A male subject roughly 55 years of age; a dermatoscopic image of a skin lesion.
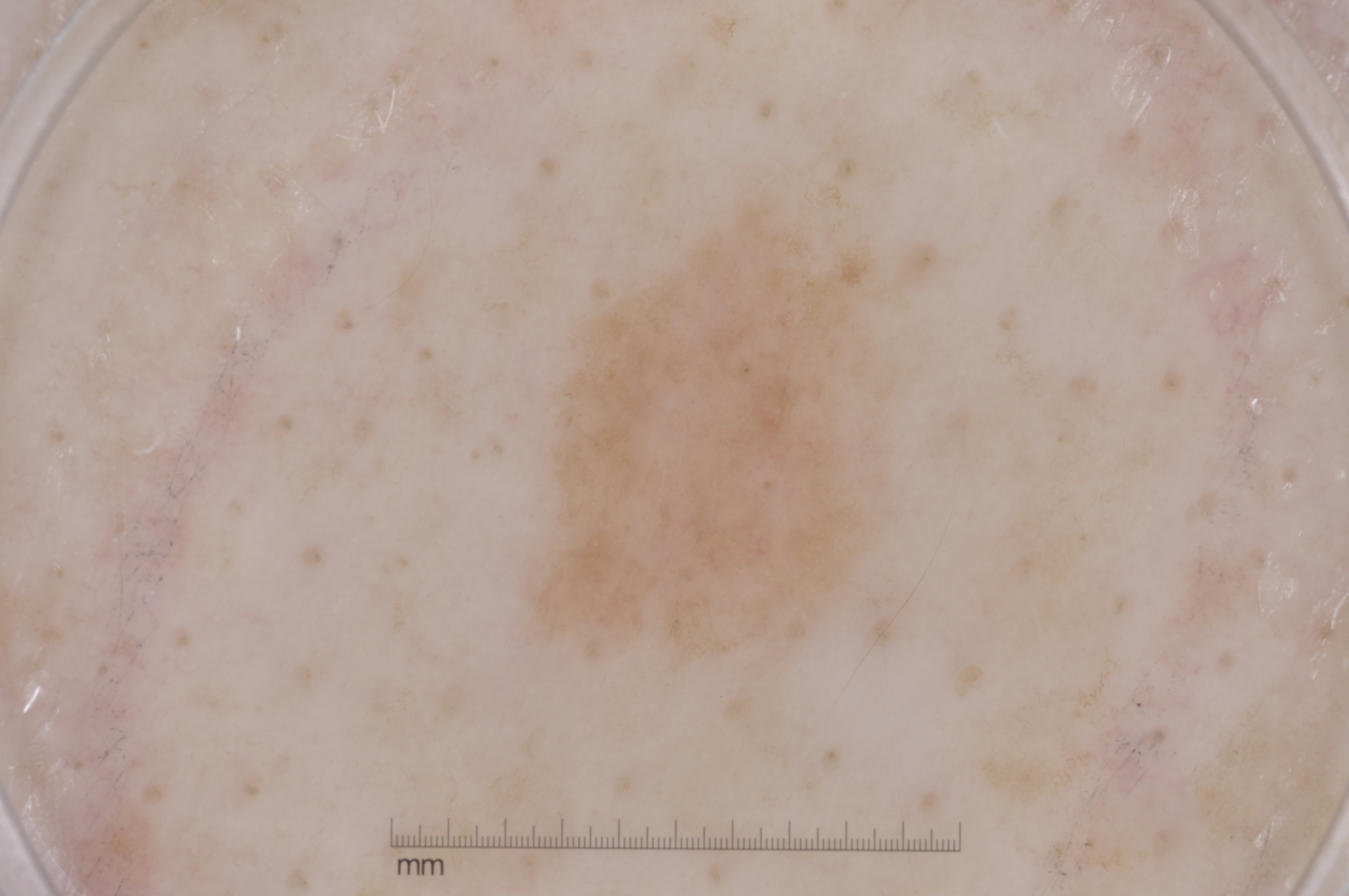A mid-sized lesion within the field.
Dermoscopically, the lesion shows no pigment network, negative network, milia-like cysts, or streaks.
With coordinates (x1, y1, x2, y2), the lesion occupies the region 527 203 896 658.
Diagnosed as a melanocytic nevus, a benign lesion.